This is a dermoscopic photograph of a skin lesion: 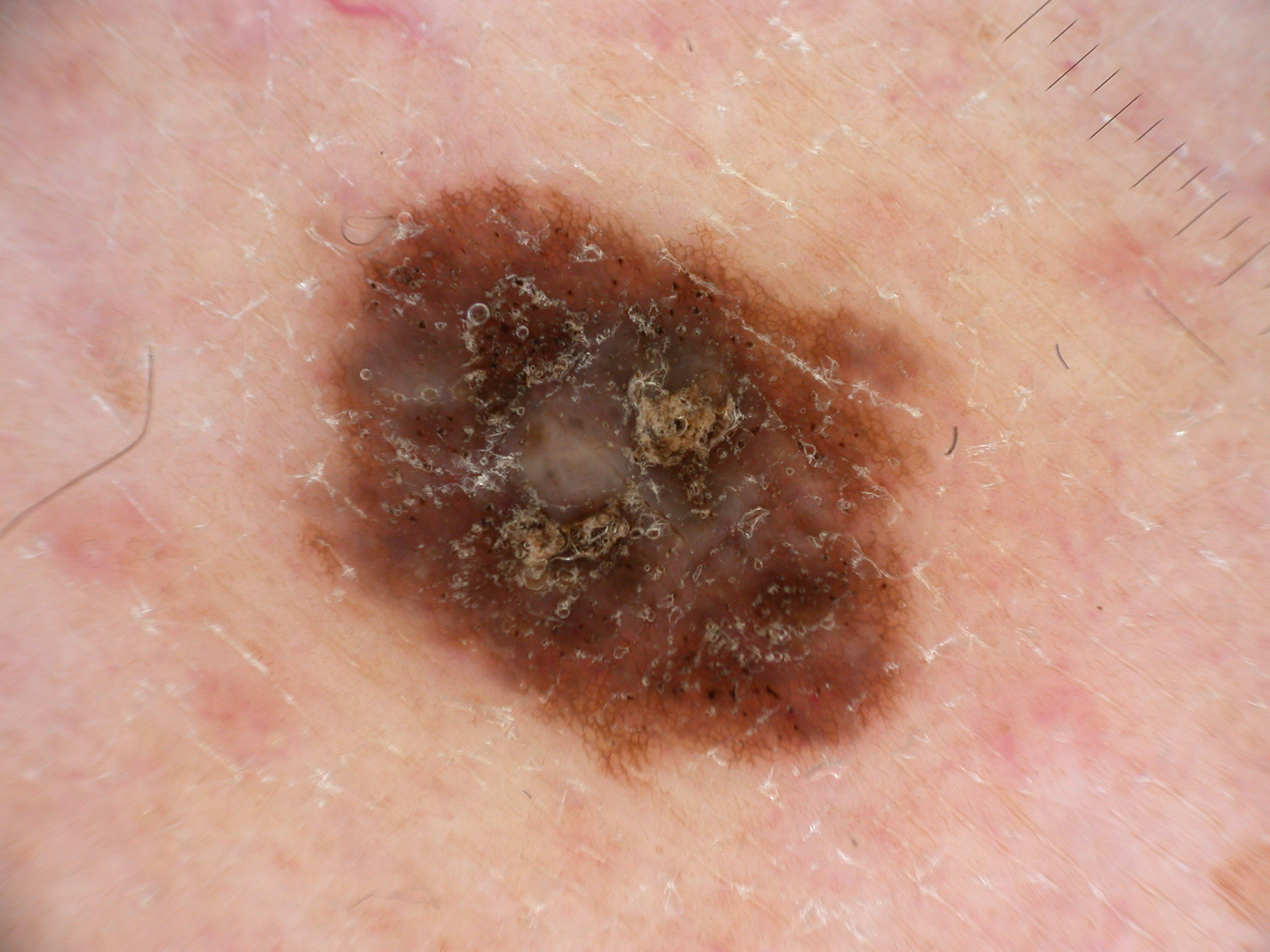Summary: As (left, top, right, bottom), lesion location: [293, 174, 979, 789]. Dermoscopically, the lesion shows pigment network. Impression: The diagnostic assessment was a melanocytic nevus.